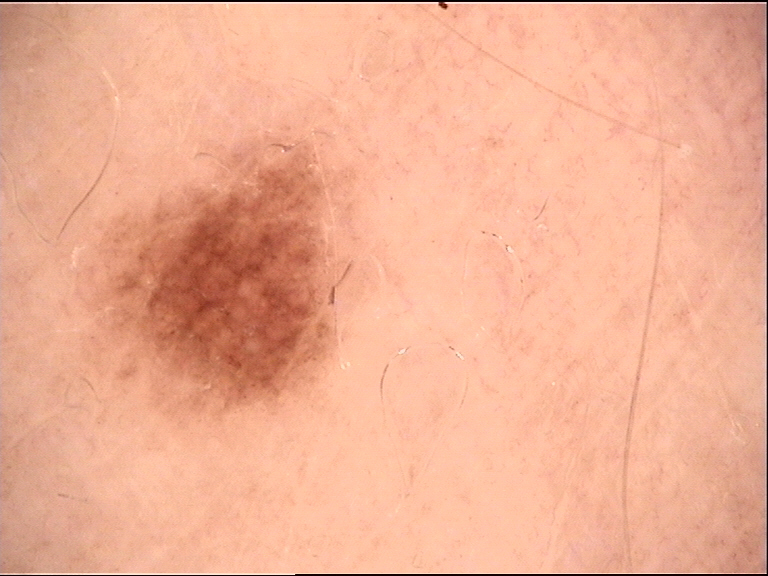image = dermatoscopy
assessment = dysplastic junctional nevus (expert consensus)